A close-up photograph:
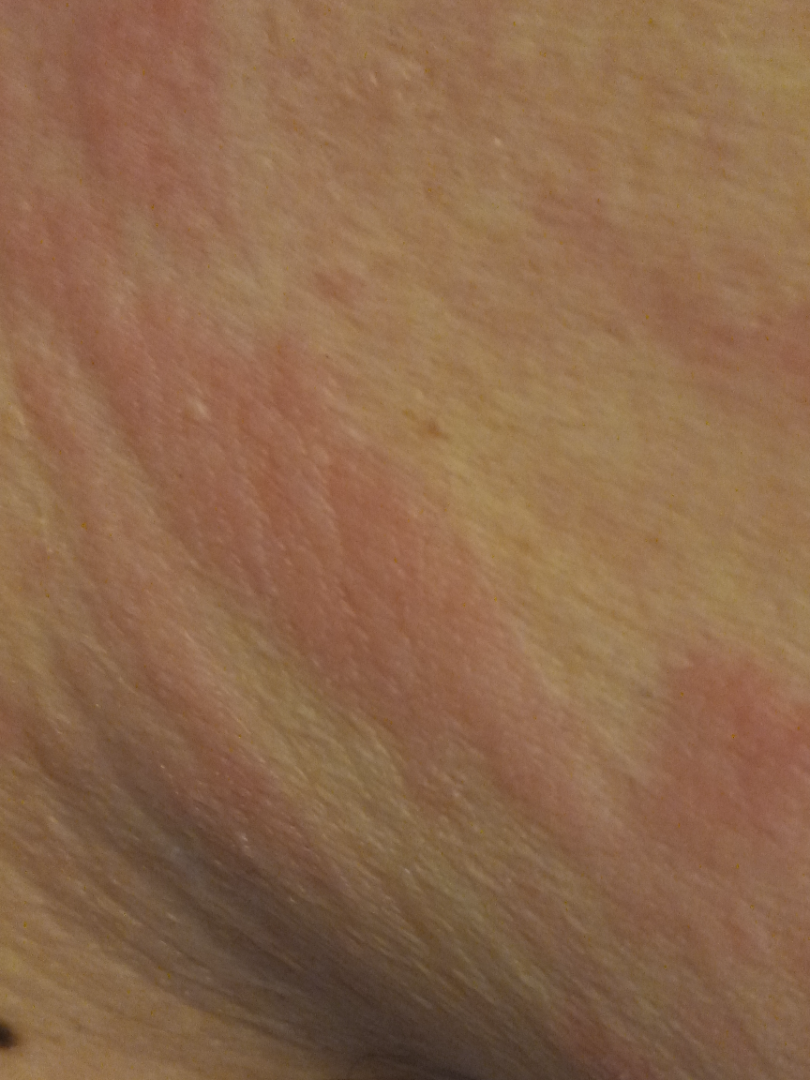| feature | finding |
|---|---|
| assessment | the impression on review was Urticaria |